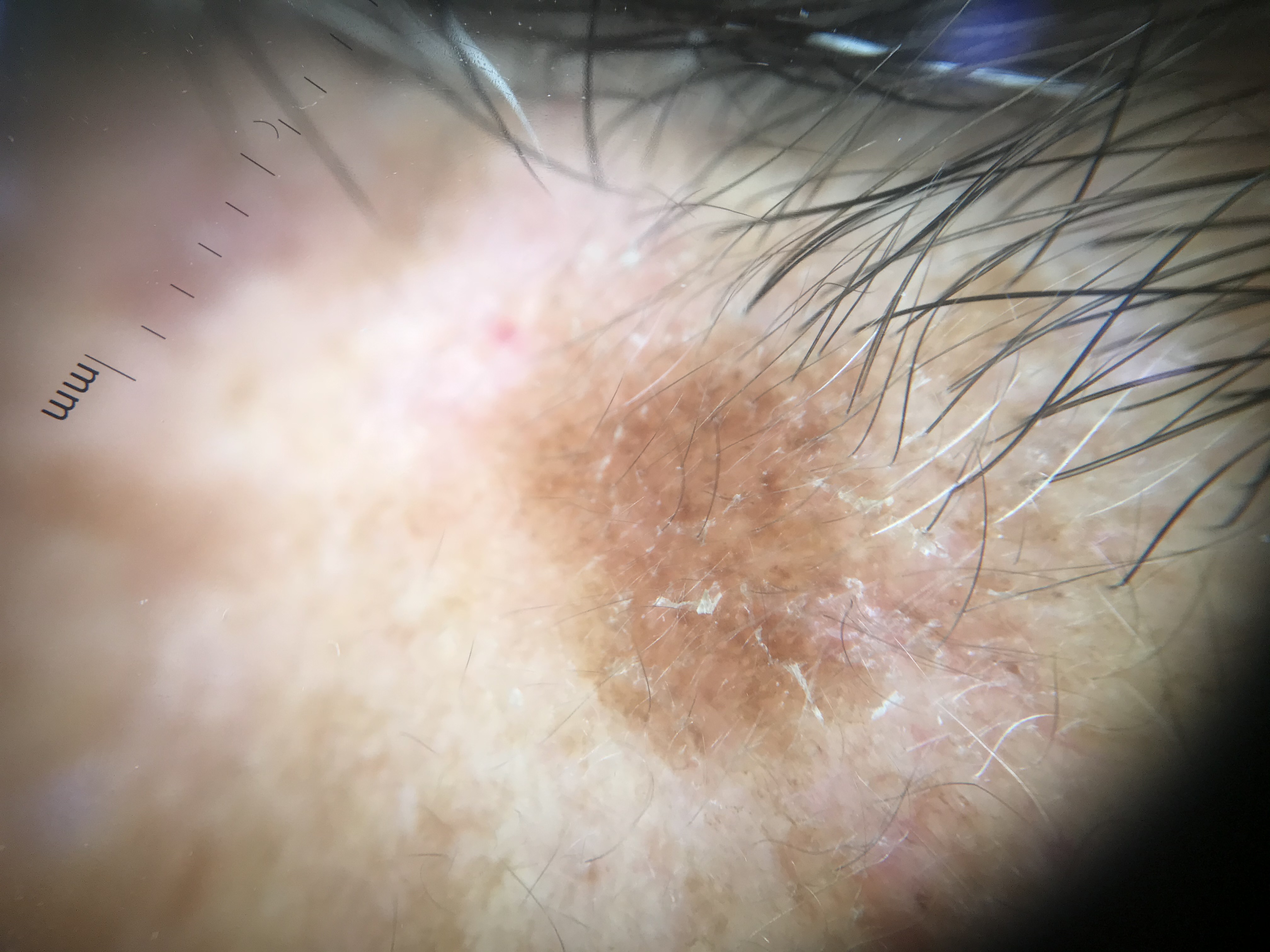A dermoscopy image of a single skin lesion. The architecture is that of a keratinocytic lesion. Consistent with a benign lesion — a seborrheic keratosis.